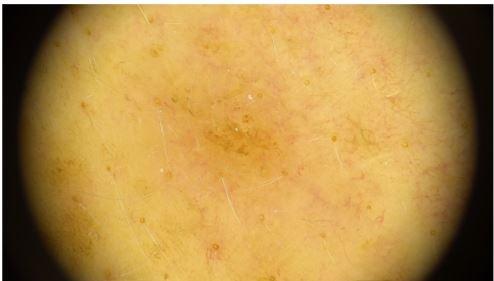Q: What is this lesion?
A: Seborrheic keratosis (clinical impression)